A dermatoscopic image of a skin lesion: 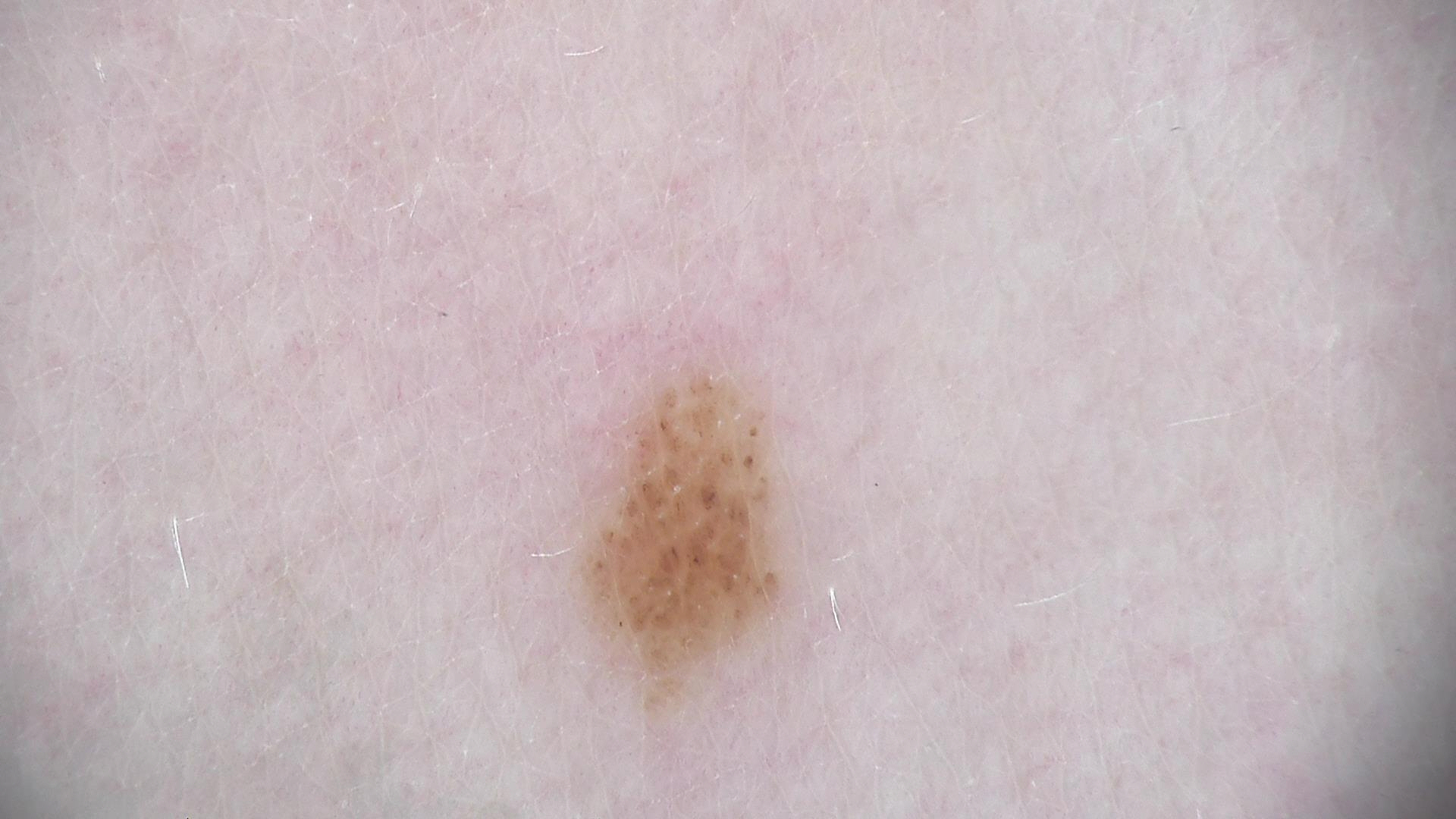Diagnosed as a banal lesion — a compound nevus.